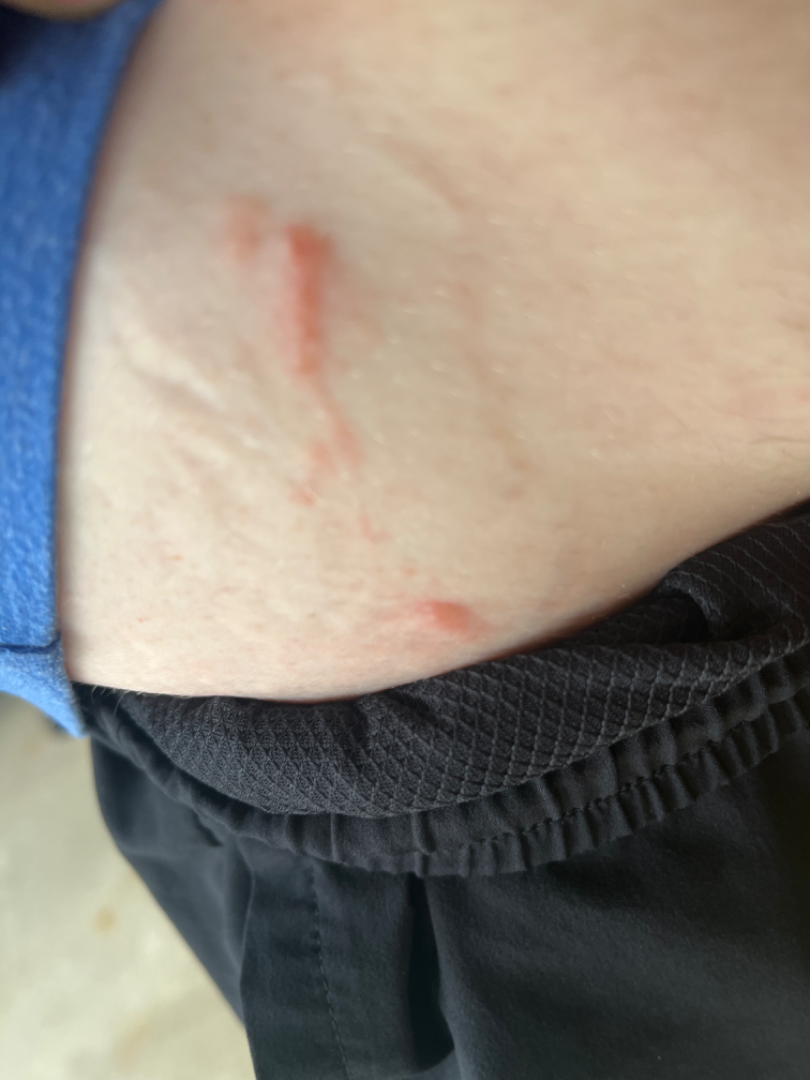| field | value |
|---|---|
| assessment | most consistent with Allergic Contact Dermatitis |